A female patient aged 68-72 · a skin lesion imaged with contact-polarized dermoscopy:
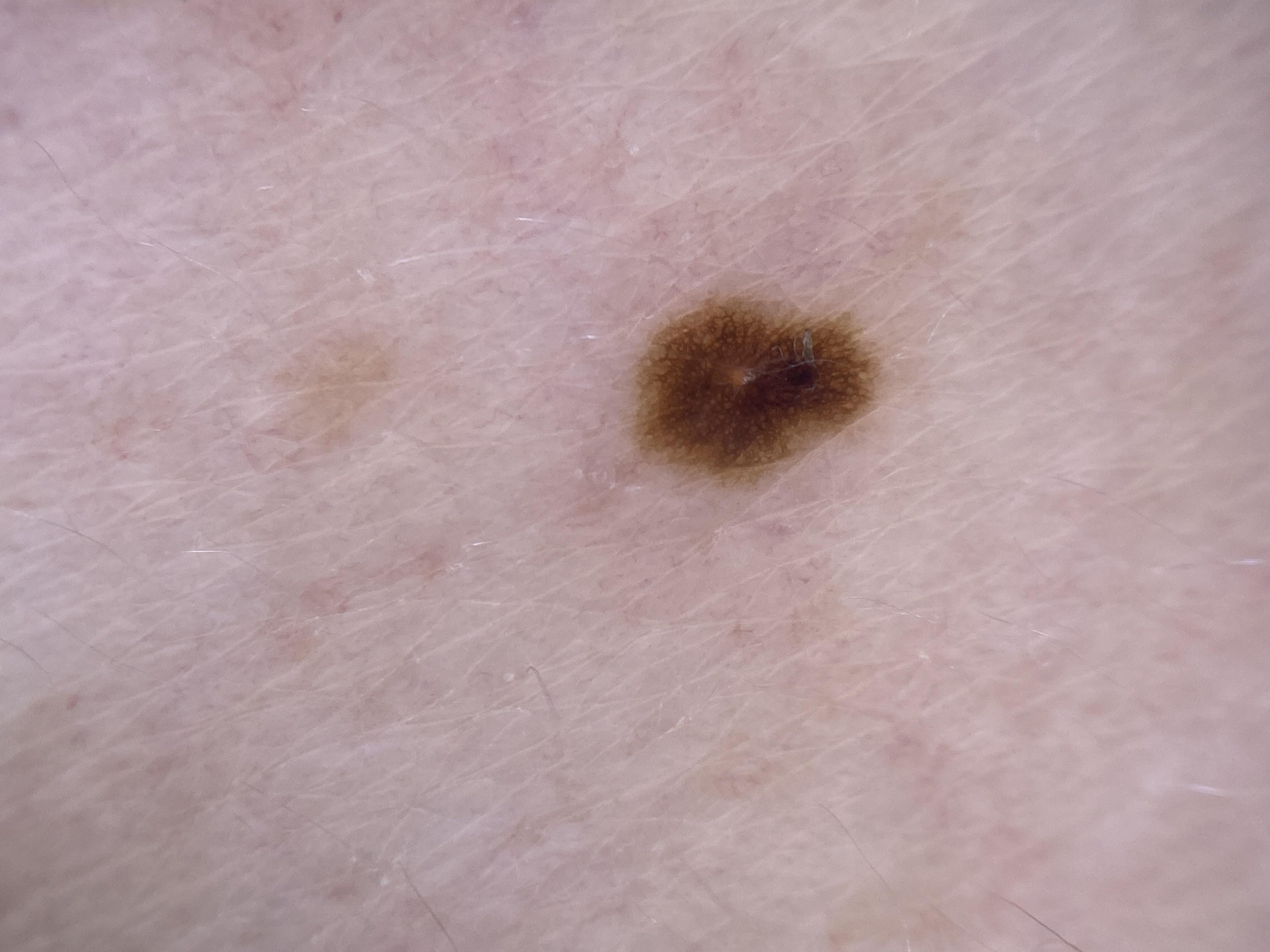The clinical assessment was a nevus.